No associated systemic symptoms reported · female contributor, age 40–49 · the patient notes the lesion is raised or bumpy · the photograph is a close-up of the affected area · the patient notes the condition has been present for less than one week · the arm is involved · the patient described the issue as a rash.
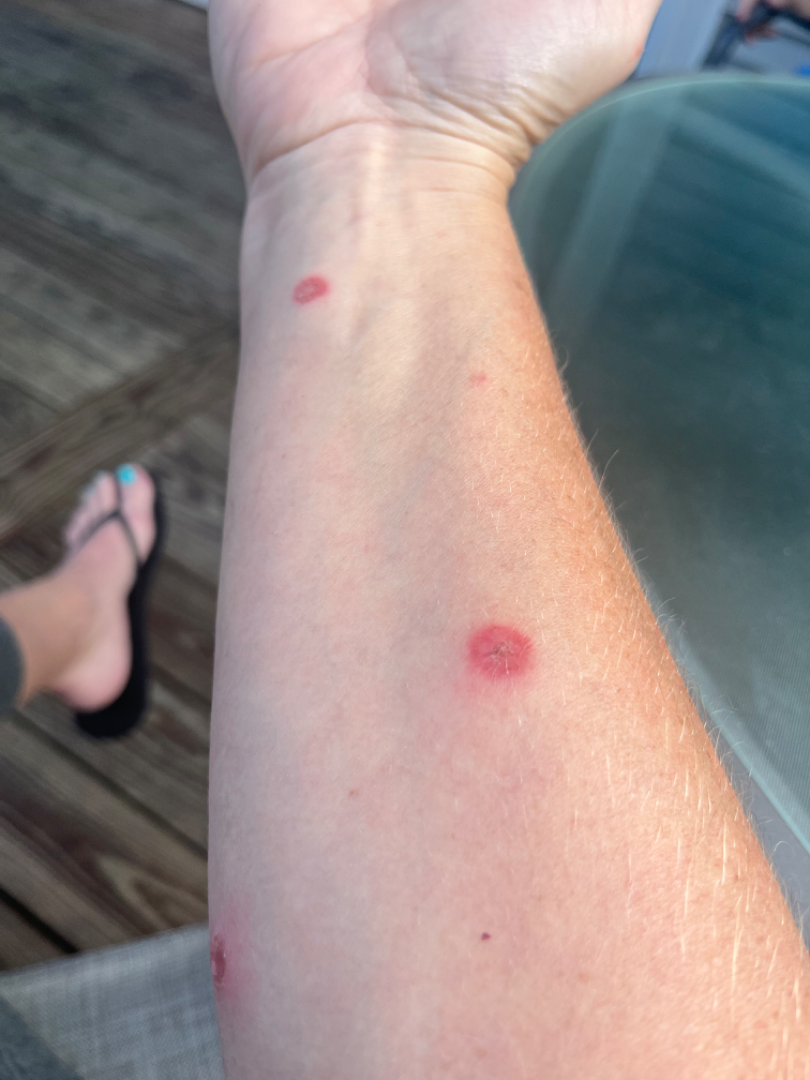Impression:
The reviewing dermatologist's impression was: Psoriasis (weight 0.33); Insect Bite (weight 0.33); Erythema multiforme (weight 0.33).